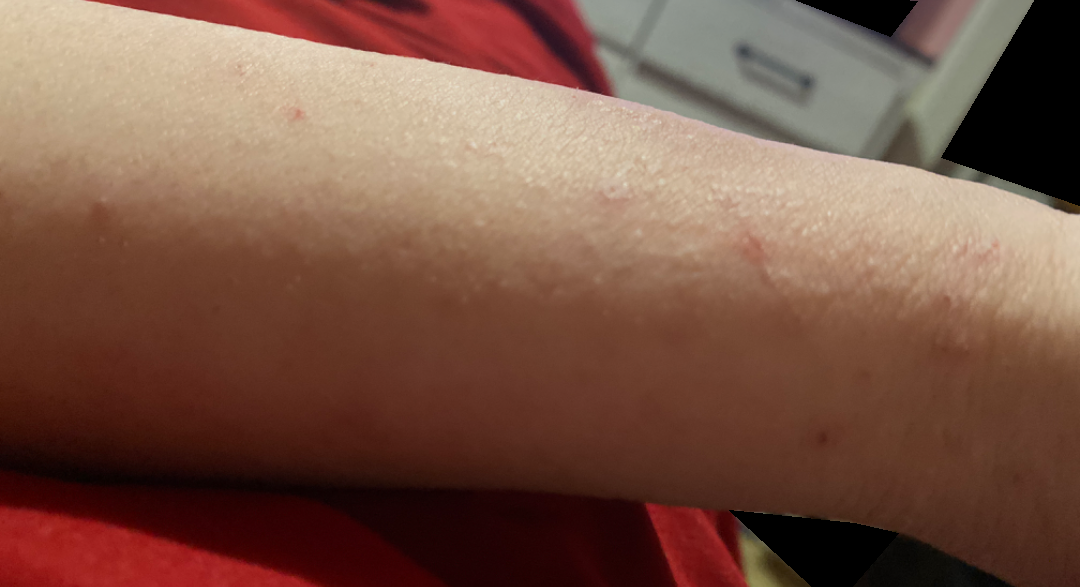An image taken at an angle. The lesion is associated with itching. The contributor is 18–29, female. Reported duration is less than one week. The lesion is described as raised or bumpy. The patient described the issue as a rash. No associated systemic symptoms reported. The arm and back of the hand are involved. Single-reviewer assessment: the leading impression is Eczema; an alternative is Allergic Contact Dermatitis.